A dermoscopic image of a skin lesion.
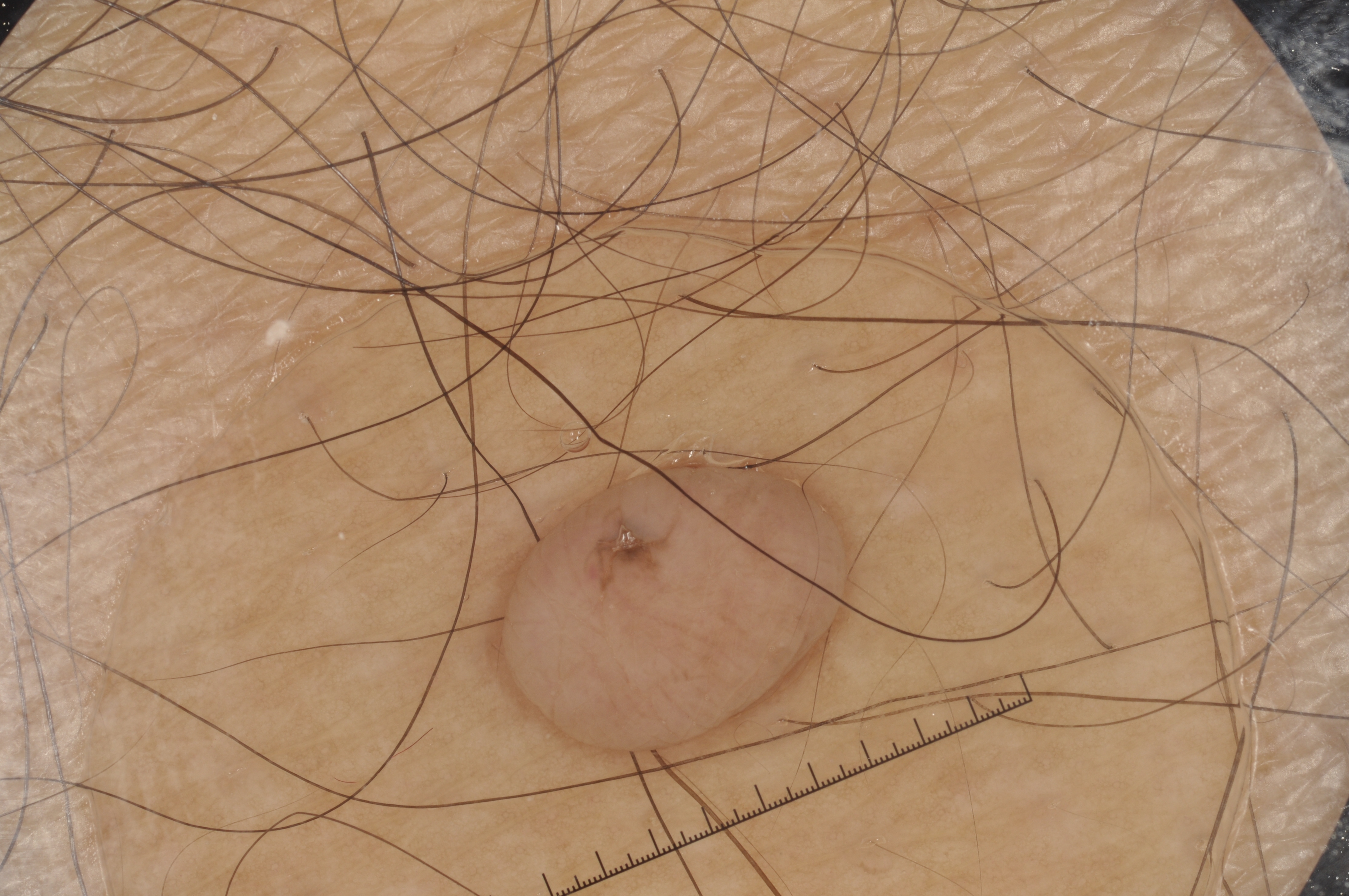Q: Where is the lesion in the image?
A: x1=494, y1=450, x2=855, y2=757
Q: What is the diagnosis?
A: a melanocytic nevus